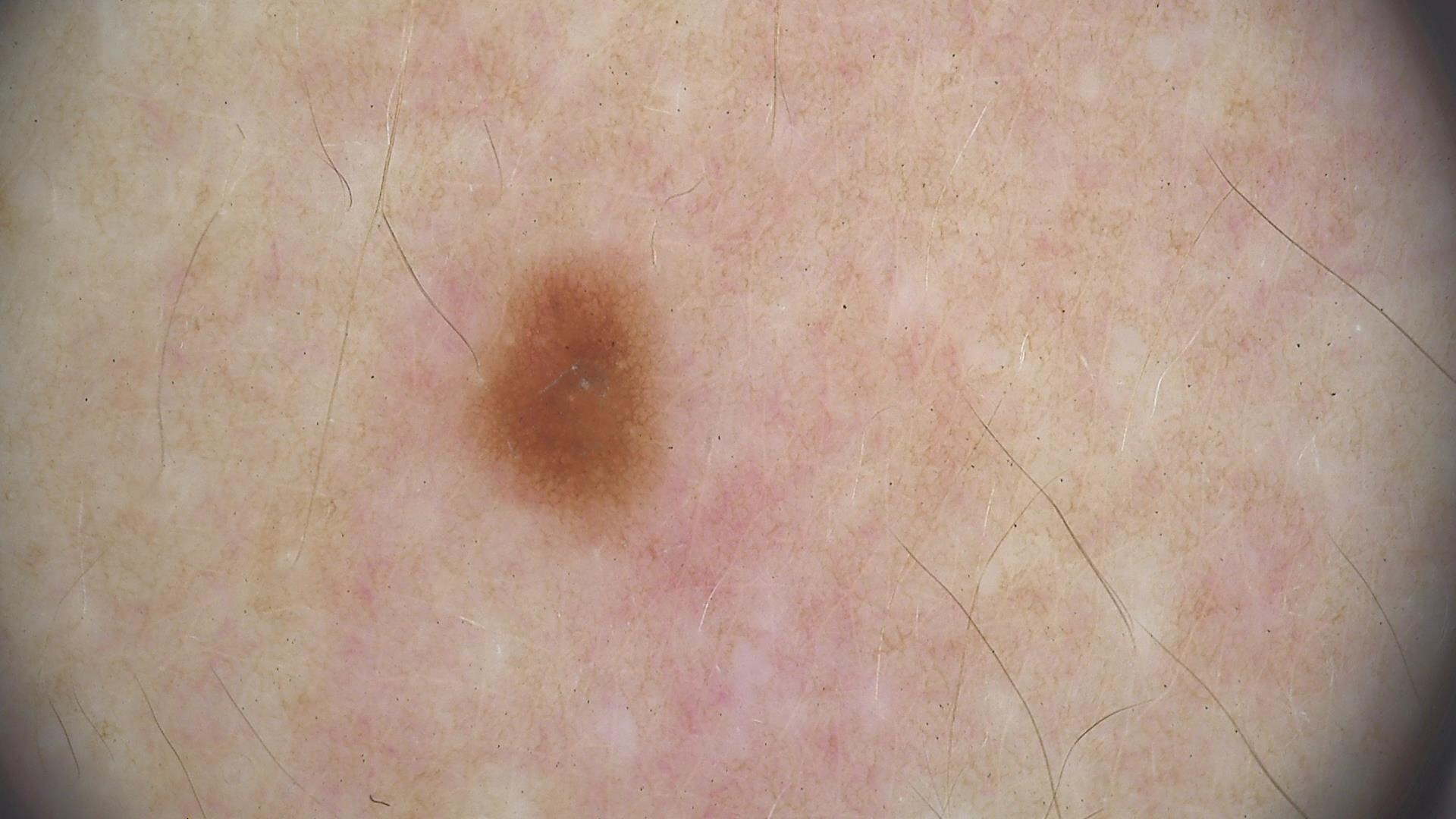image type=dermoscopy
diagnostic label=junctional nevus (expert consensus)